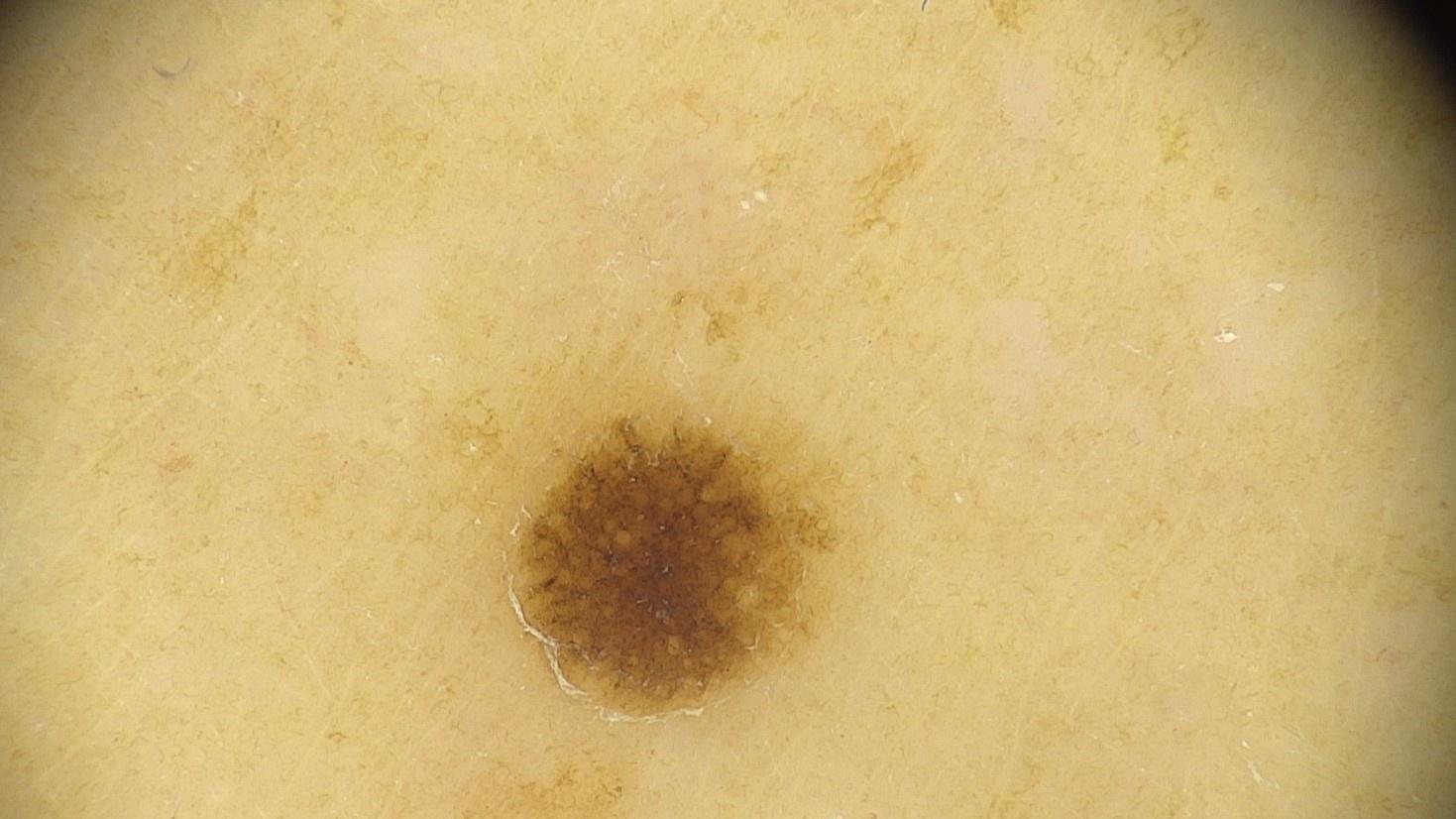melanoma history = a prior melanoma but no first-degree relative with melanoma; FST = II; anatomic site = a lower extremity; diagnosis = Melanoma (biopsy-proven).